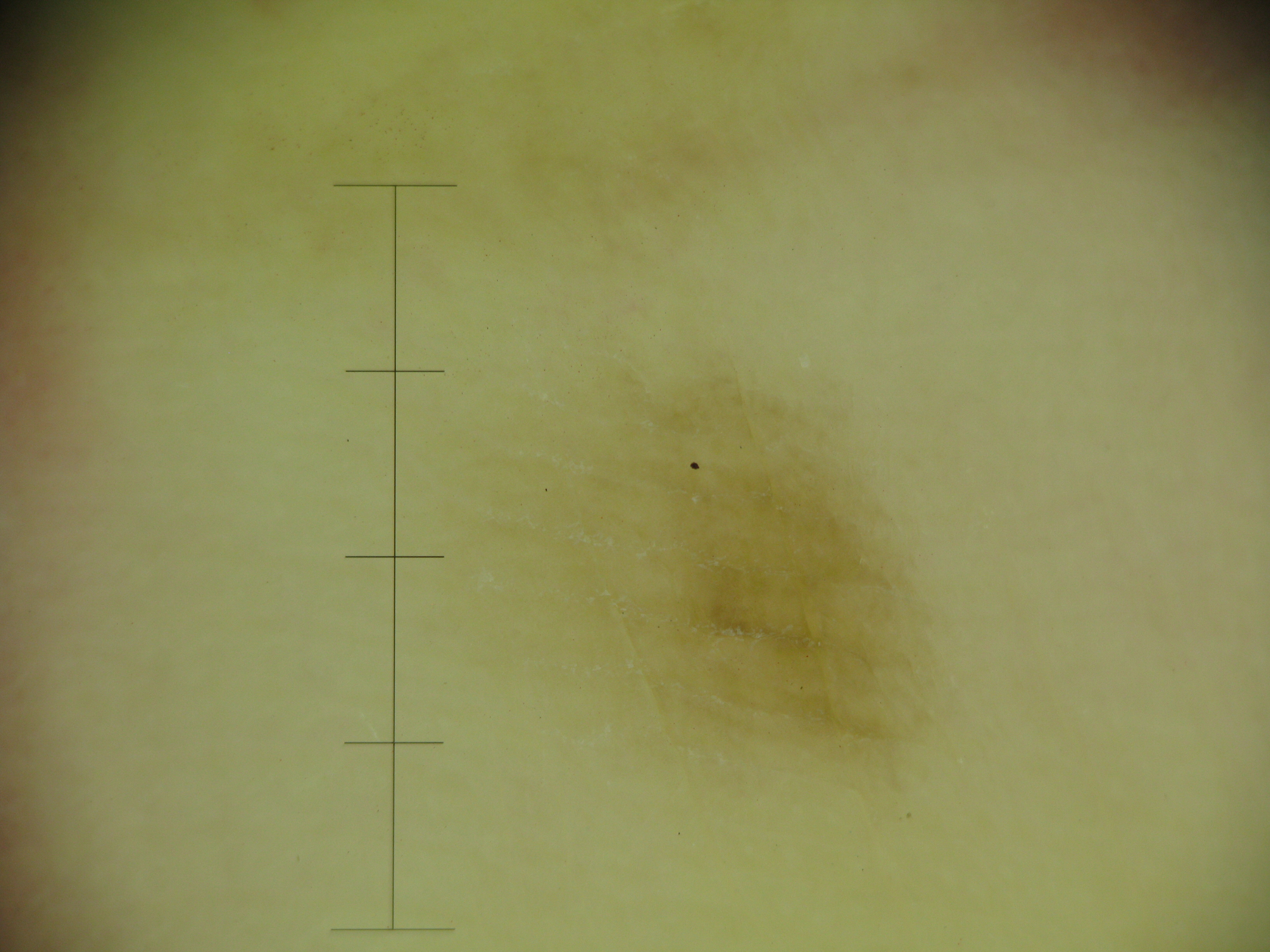Summary:
A dermoscopy image of a single skin lesion. The architecture is that of a banal lesion.
Conclusion:
The diagnostic label was an acral junctional nevus.